Dermoscopy of a skin lesion.
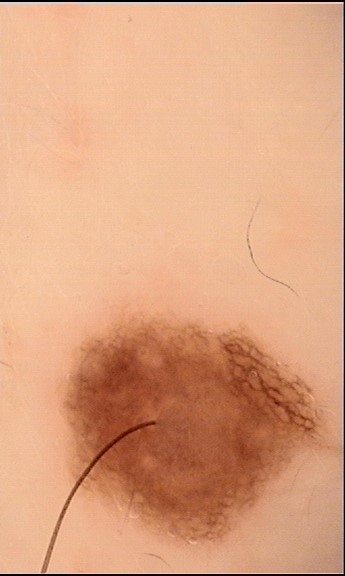{"diagnosis": {"name": "dysplastic compound nevus", "code": "cd", "malignancy": "benign", "super_class": "melanocytic", "confirmation": "expert consensus"}}